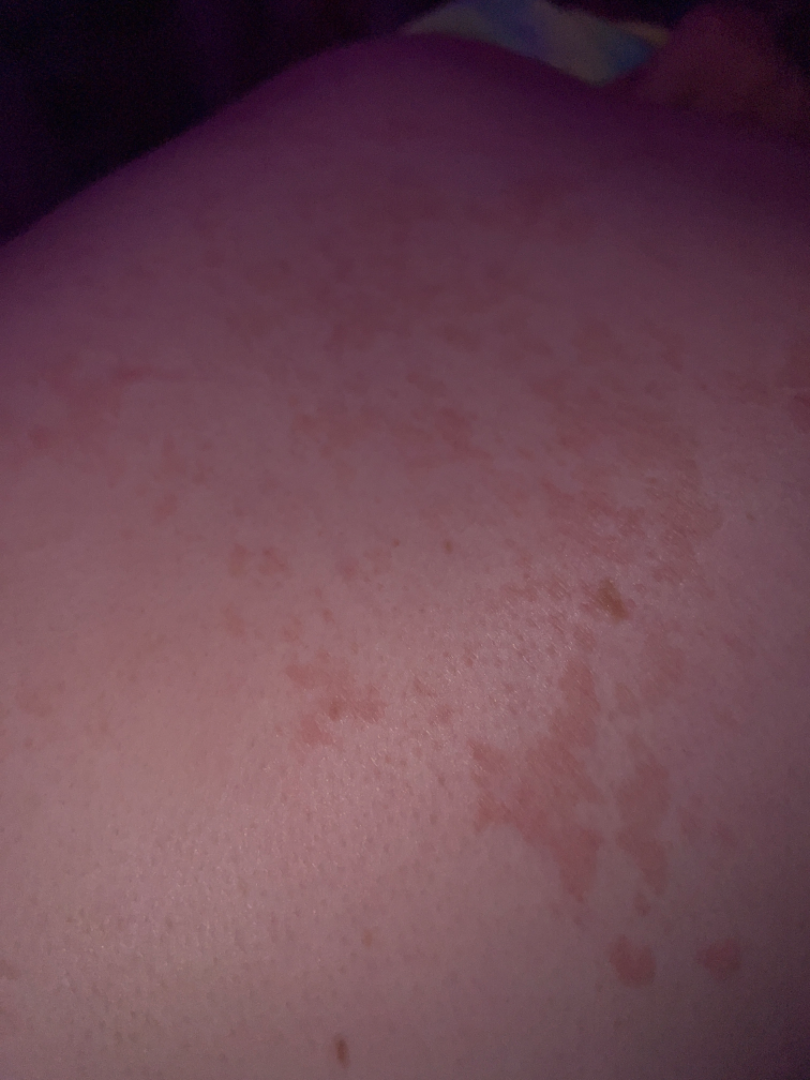The skin condition could not be confidently assessed from this image.